A dermatoscopic image of a skin lesion: 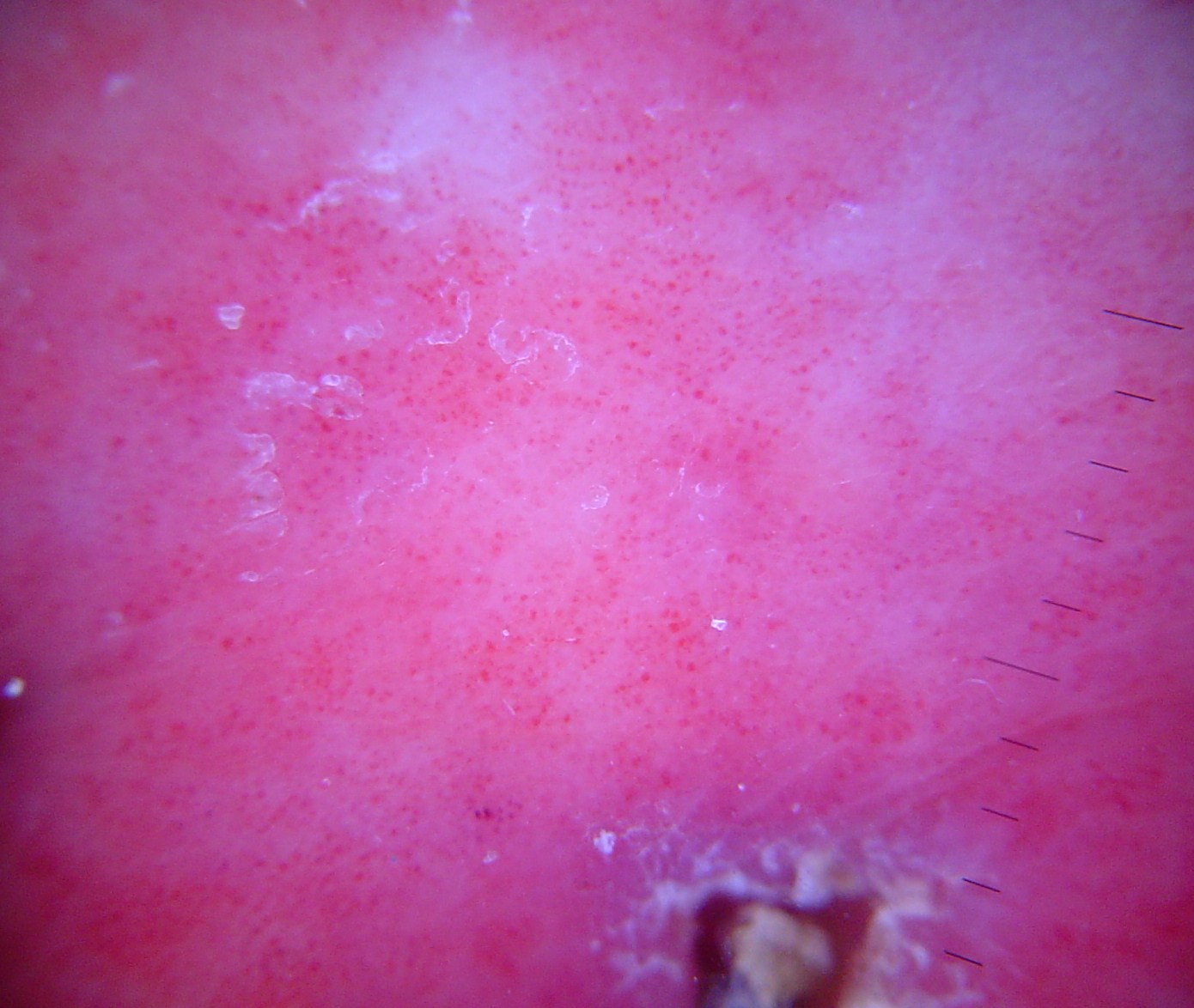The morphology is that of a vascular lesion. Diagnosed as a hemangioma.